Close-up view. The back of the hand is involved.
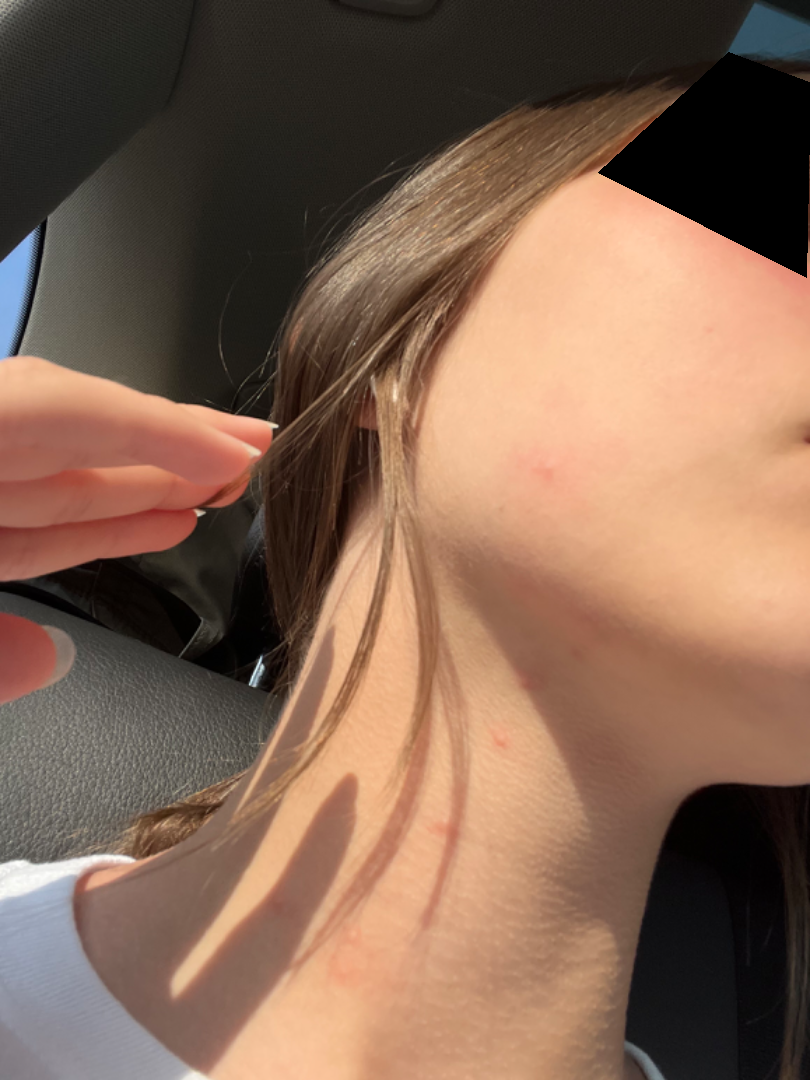Impression:
The dermatologist could not determine a likely condition from the photograph alone.